Located on the arm and front of the torso, an image taken at an angle:
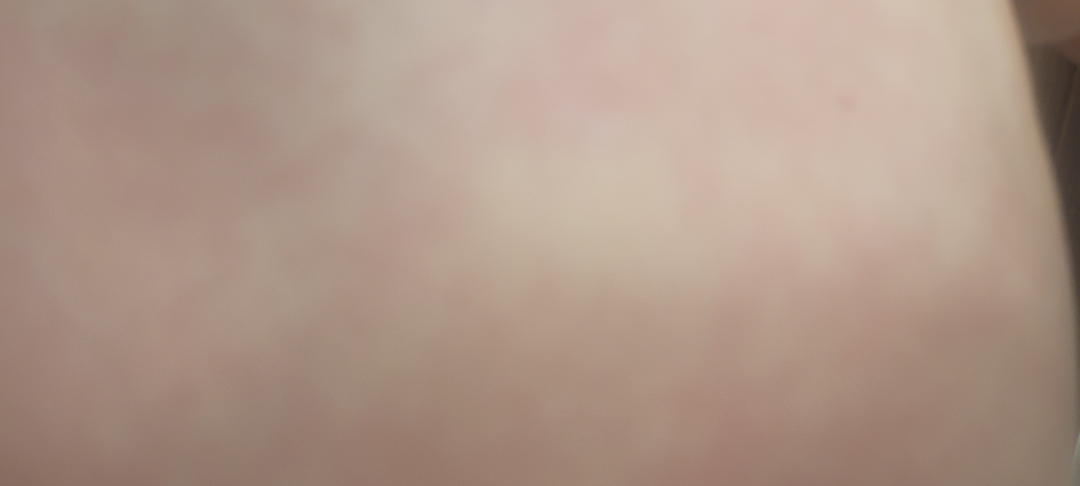Case summary:
- assessment · could not be assessed
- patient's own categorization · a rash